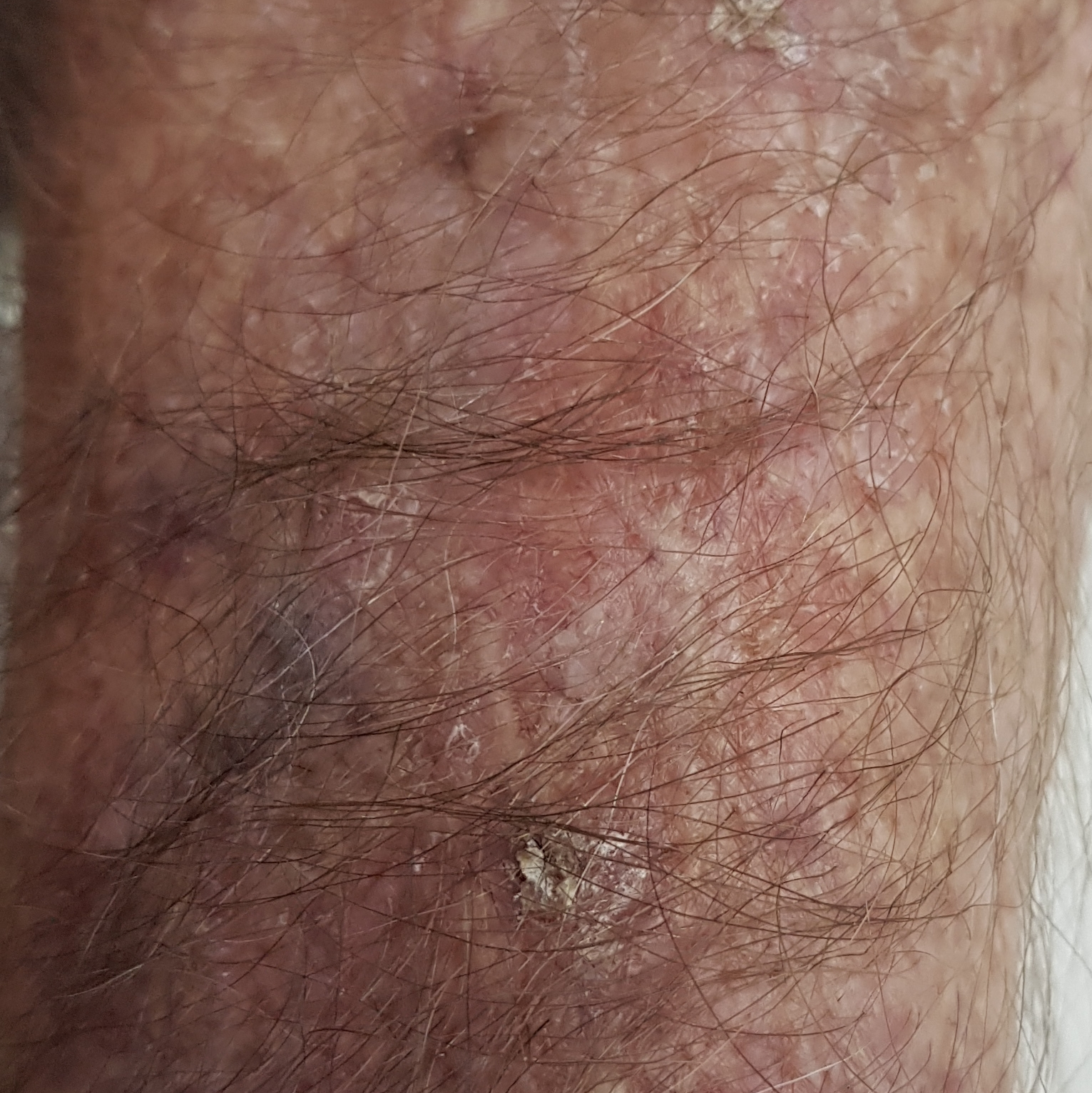Patient and lesion:
A patient in their late 70s. A clinical photograph of a skin lesion. The patient reports that the lesion is elevated, has grown, and itches.
Impression:
Expert review favored an actinic keratosis.